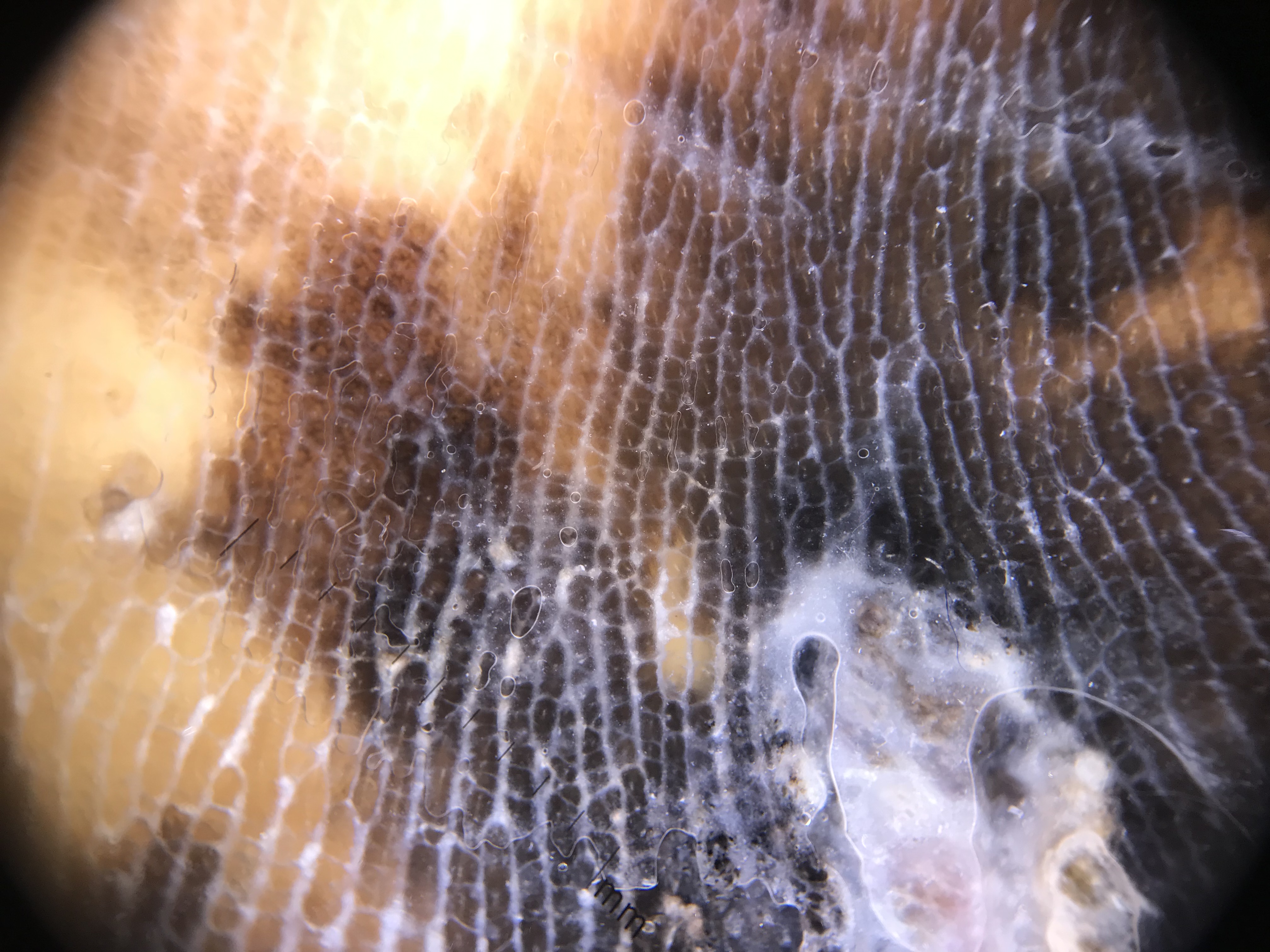Q: What is the imaging modality?
A: dermoscopy
Q: What is this lesion?
A: acral lentiginous melanoma (biopsy-proven)